The affected area is the arm; the subject is a male aged 30–39; an image taken at an angle:
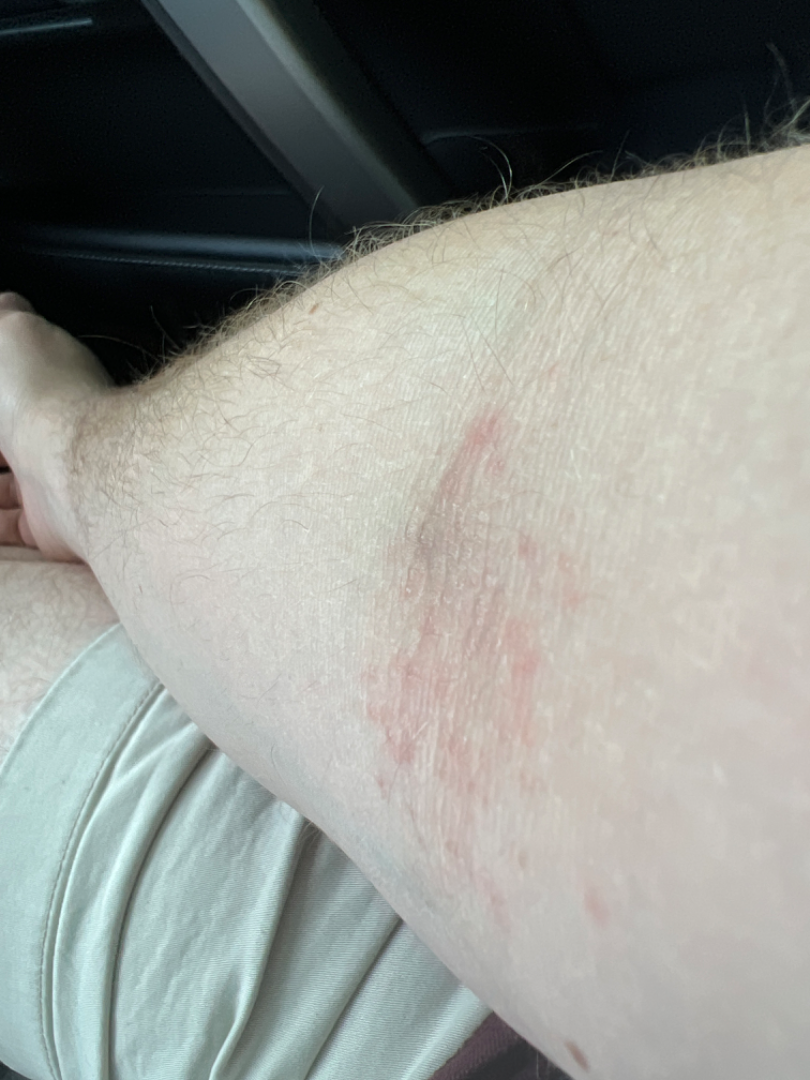Q: Any systemic symptoms?
A: none reported
Q: Reported symptoms?
A: itching and darkening
Q: When did this start?
A: one to four weeks
Q: What is the differential diagnosis?
A: most consistent with Eczema; less likely is Allergic Contact Dermatitis